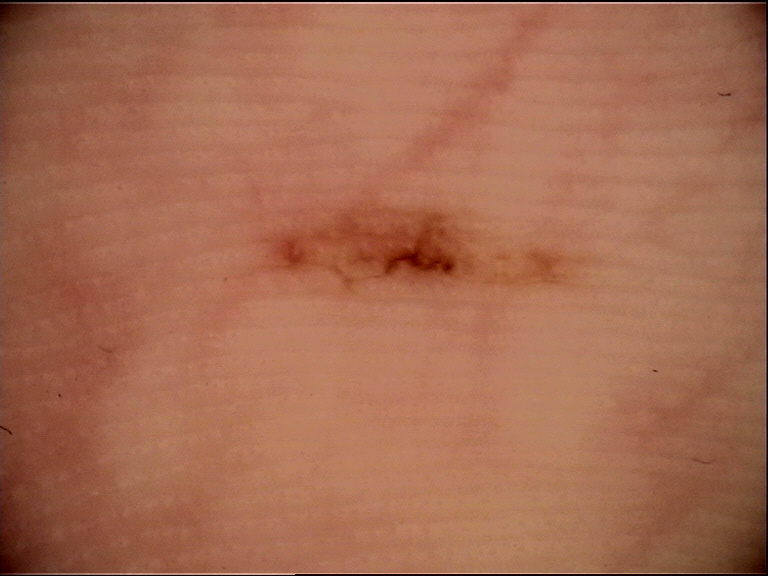Summary: A dermatoscopic image of a skin lesion. Conclusion: Classified as a benign lesion — an acral dysplastic junctional nevus.